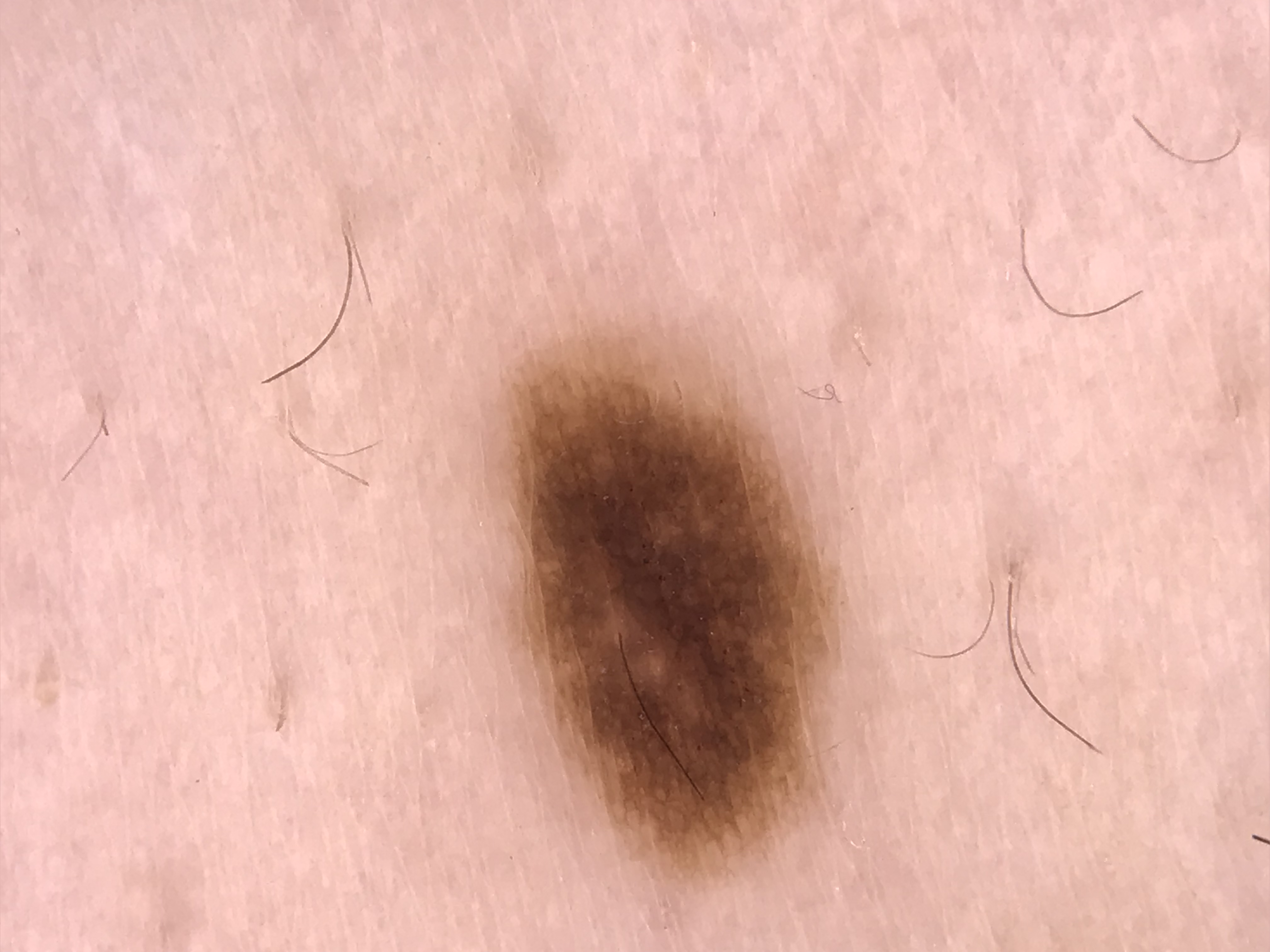A dermatoscopic image of a skin lesion.
Labeled as a benign lesion — a dysplastic junctional nevus.